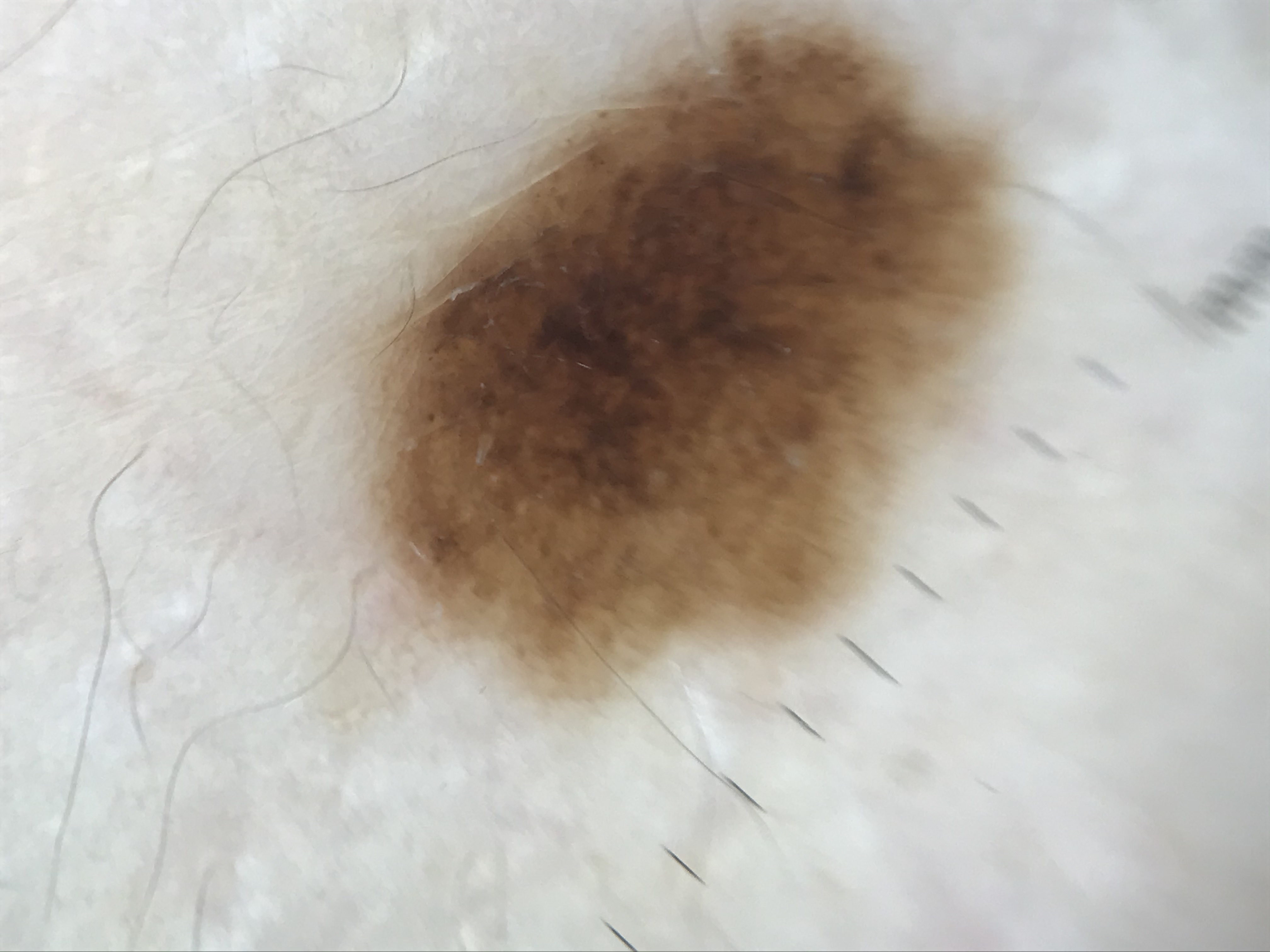A dermoscopic close-up of a skin lesion.
Classified as a benign lesion — a dysplastic compound nevus.